A dermoscopic photograph of a skin lesion.
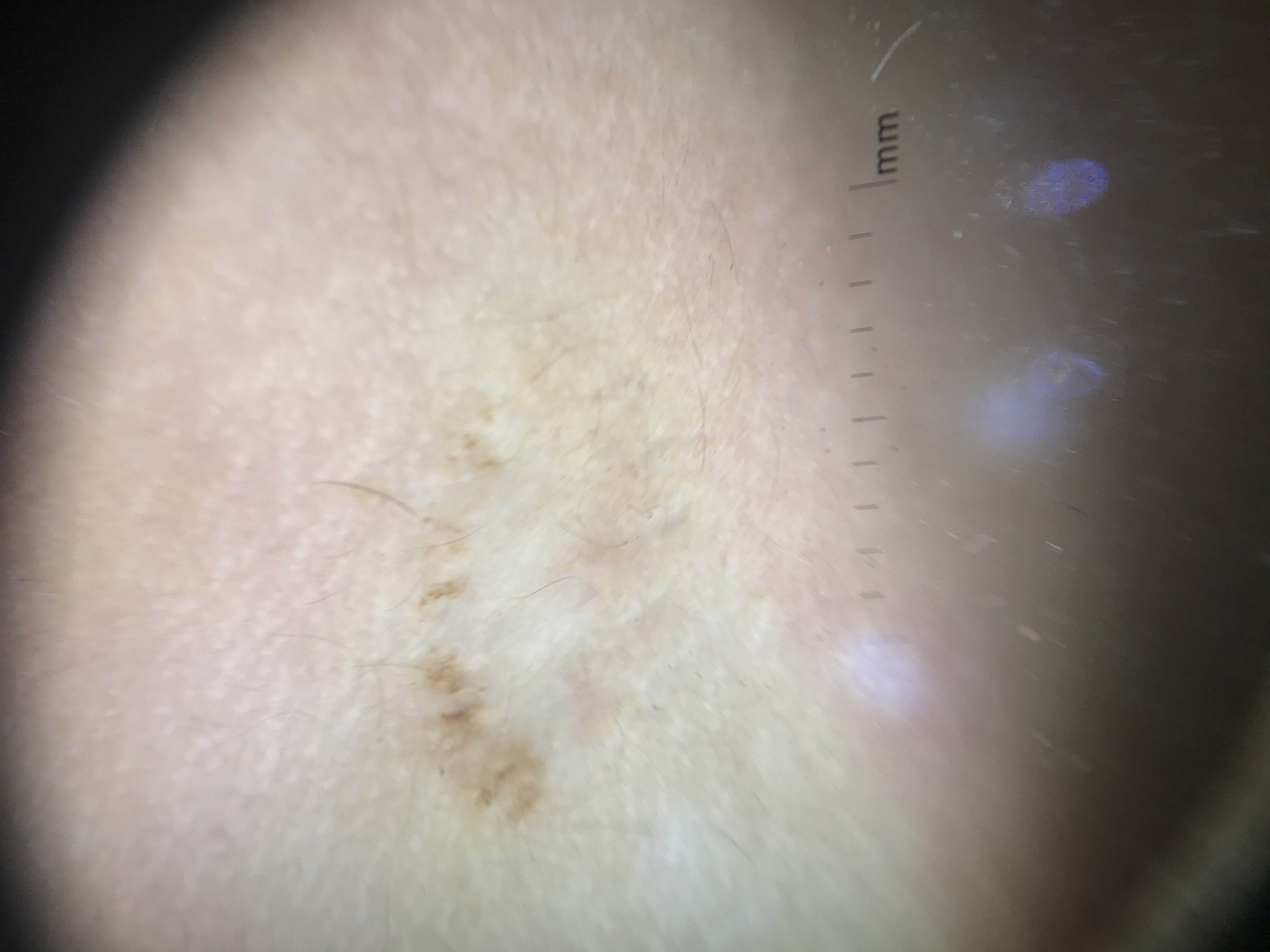<dermoscopy>
  <lesion_type>
    <main_class>dysplastic</main_class>
    <pattern>recurrent</pattern>
  </lesion_type>
  <diagnosis>
    <name>recurrent nevus</name>
    <code>rd</code>
    <malignancy>benign</malignancy>
    <super_class>melanocytic</super_class>
    <confirmation>expert consensus</confirmation>
  </diagnosis>
</dermoscopy>